A dermoscopic view of a skin lesion.
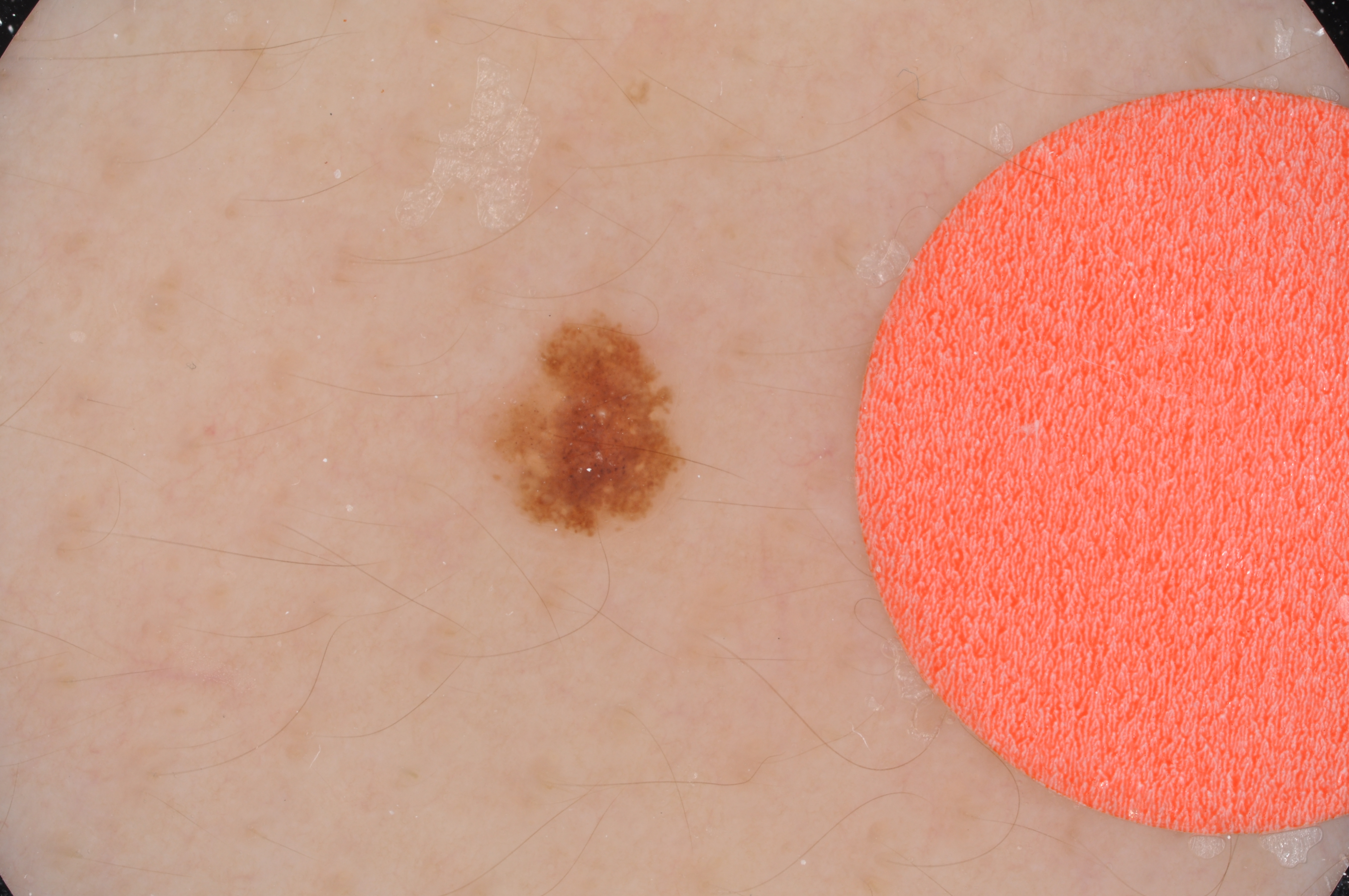Q: How much of the field does the lesion occupy?
A: ~3% of the field
Q: Where is the lesion in the image?
A: [474, 305, 691, 550]
Q: What dermoscopic features are present?
A: milia-like cysts, globules, and pigment network
Q: What is this lesion?
A: a melanocytic nevus